A dermoscopic image of a skin lesion.
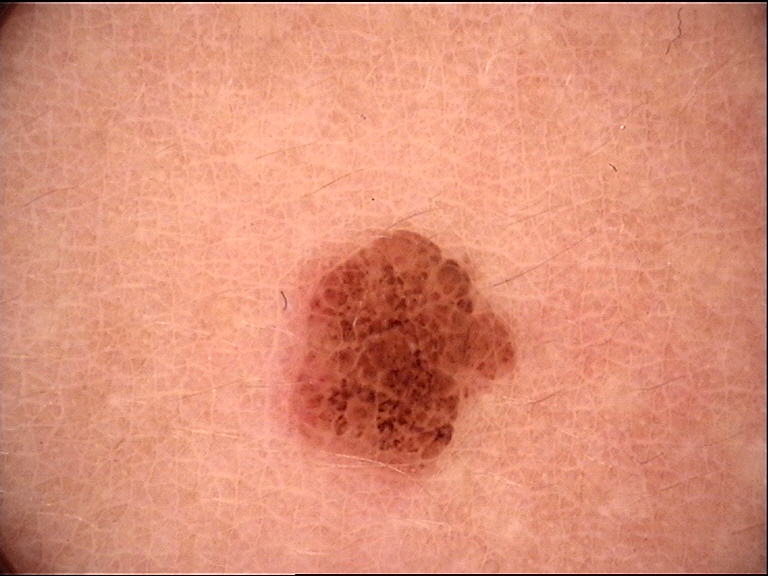This is a banal lesion.
The diagnosis was a compound nevus.